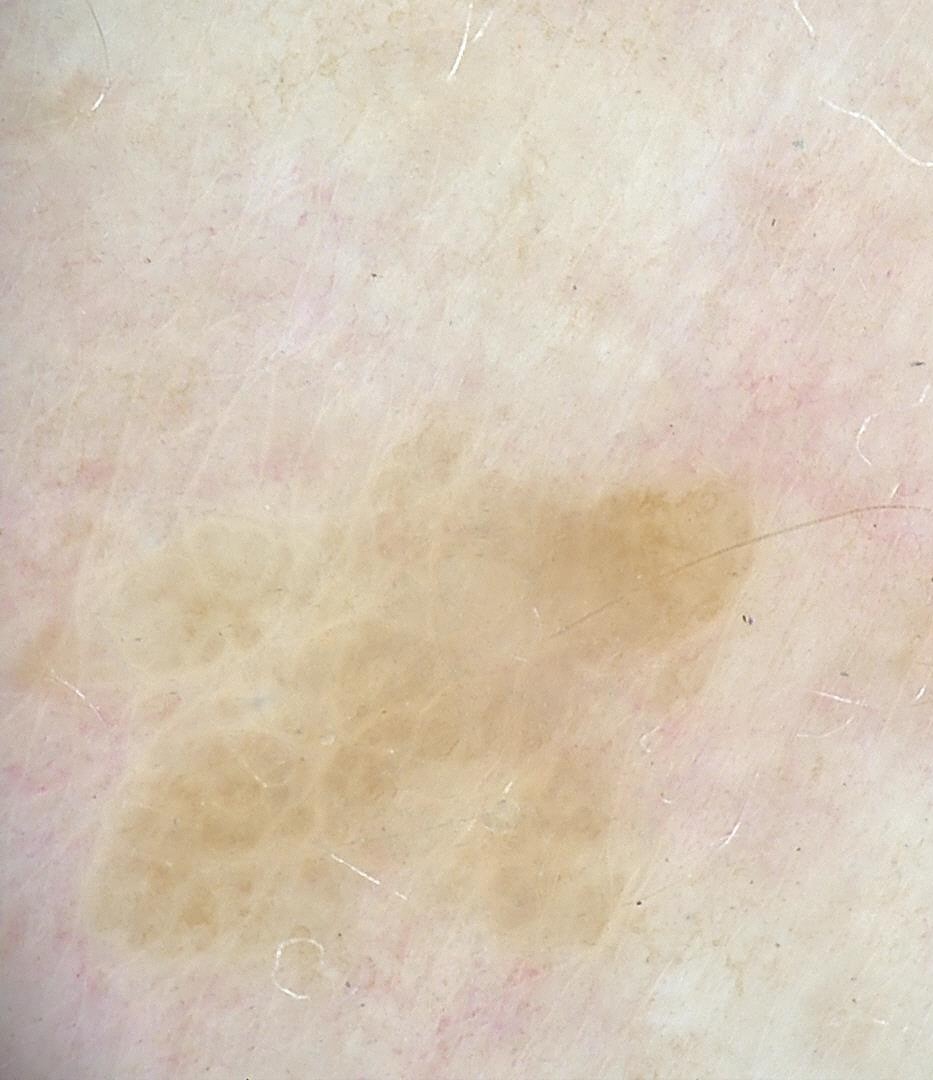Diagnosed as a seborrheic keratosis.